A dermoscopic close-up of a skin lesion.
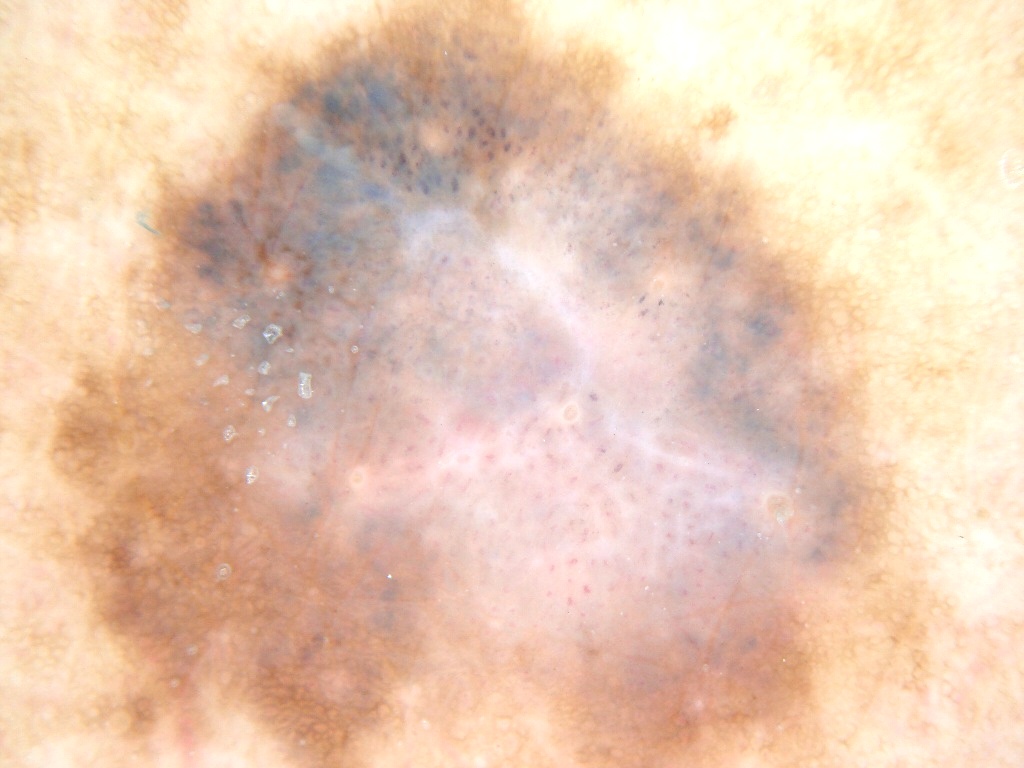<case>
  <lesion_location>
    <bbox_xyxy>41, 2, 932, 766</bbox_xyxy>
  </lesion_location>
  <lesion_extent>large</lesion_extent>
  <diagnosis>
    <malignancy>benign</malignancy>
    <provenance>clinical</provenance>
  </diagnosis>
</case>